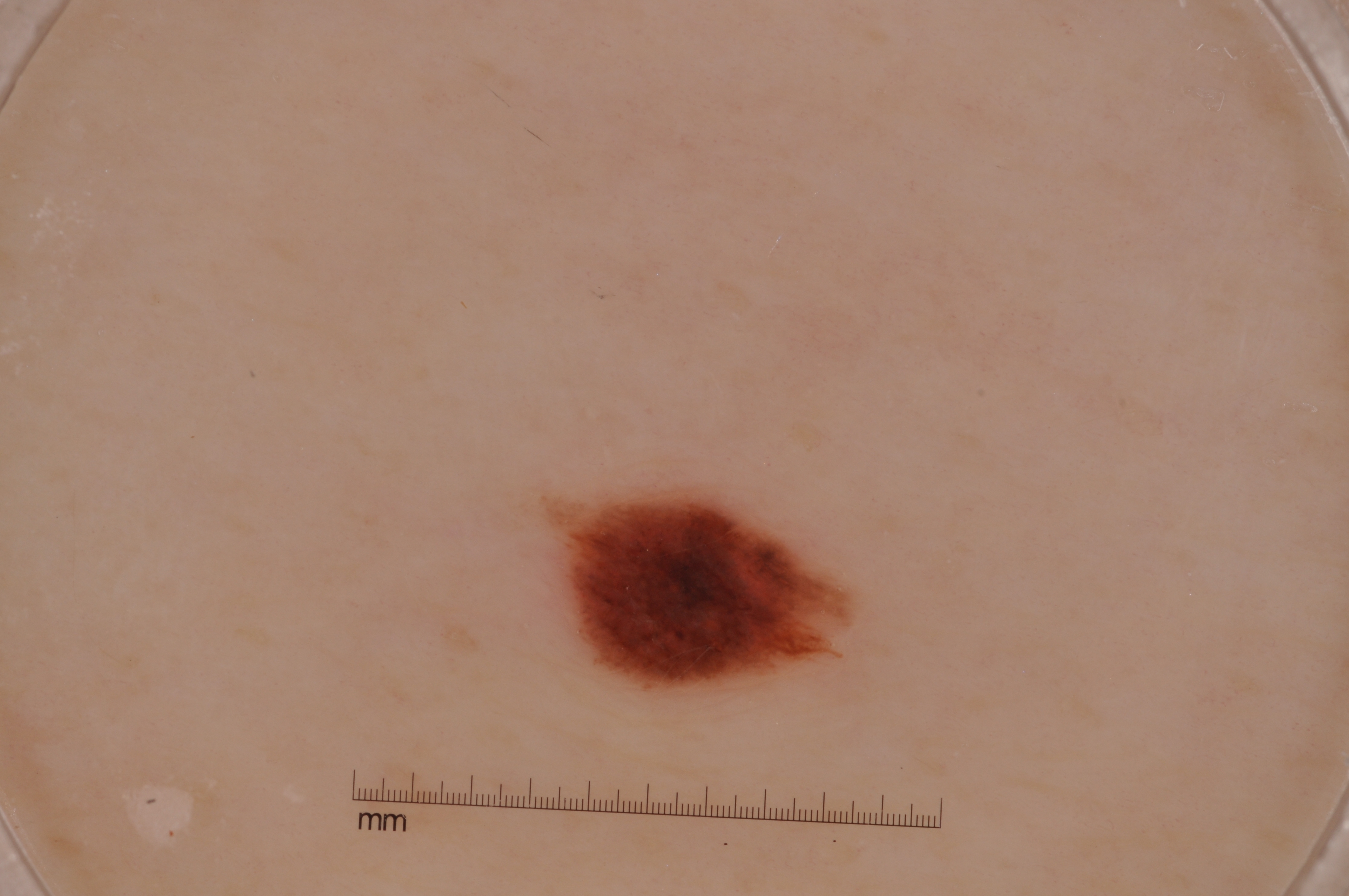image = dermoscopic image | lesion location = box(548, 483, 854, 693) | assessment = a melanoma, a skin cancer.